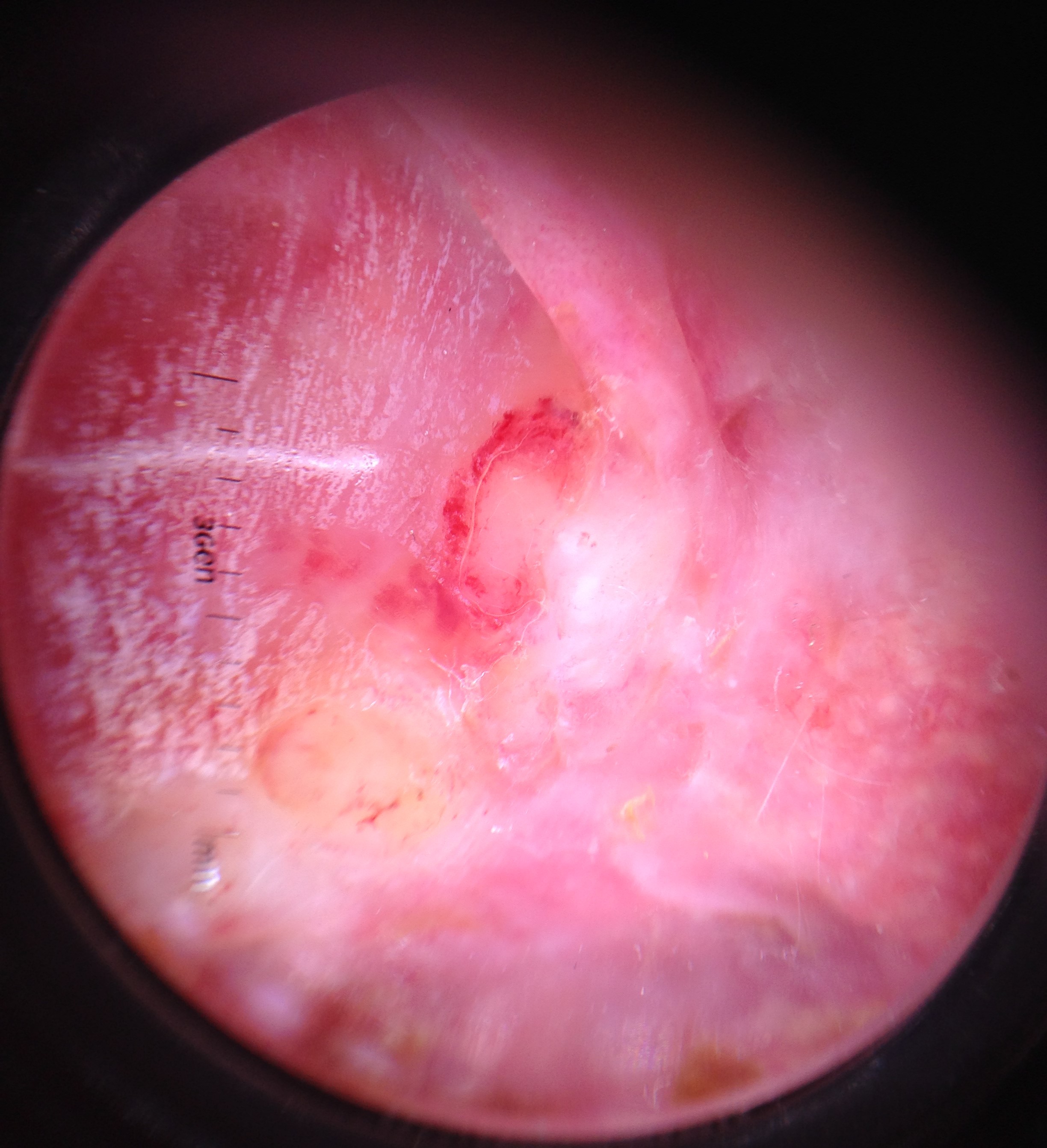Confirmed on histopathology as a squamous cell carcinoma.